A clinical close-up photograph of a skin lesion. A subject in their early 60s:
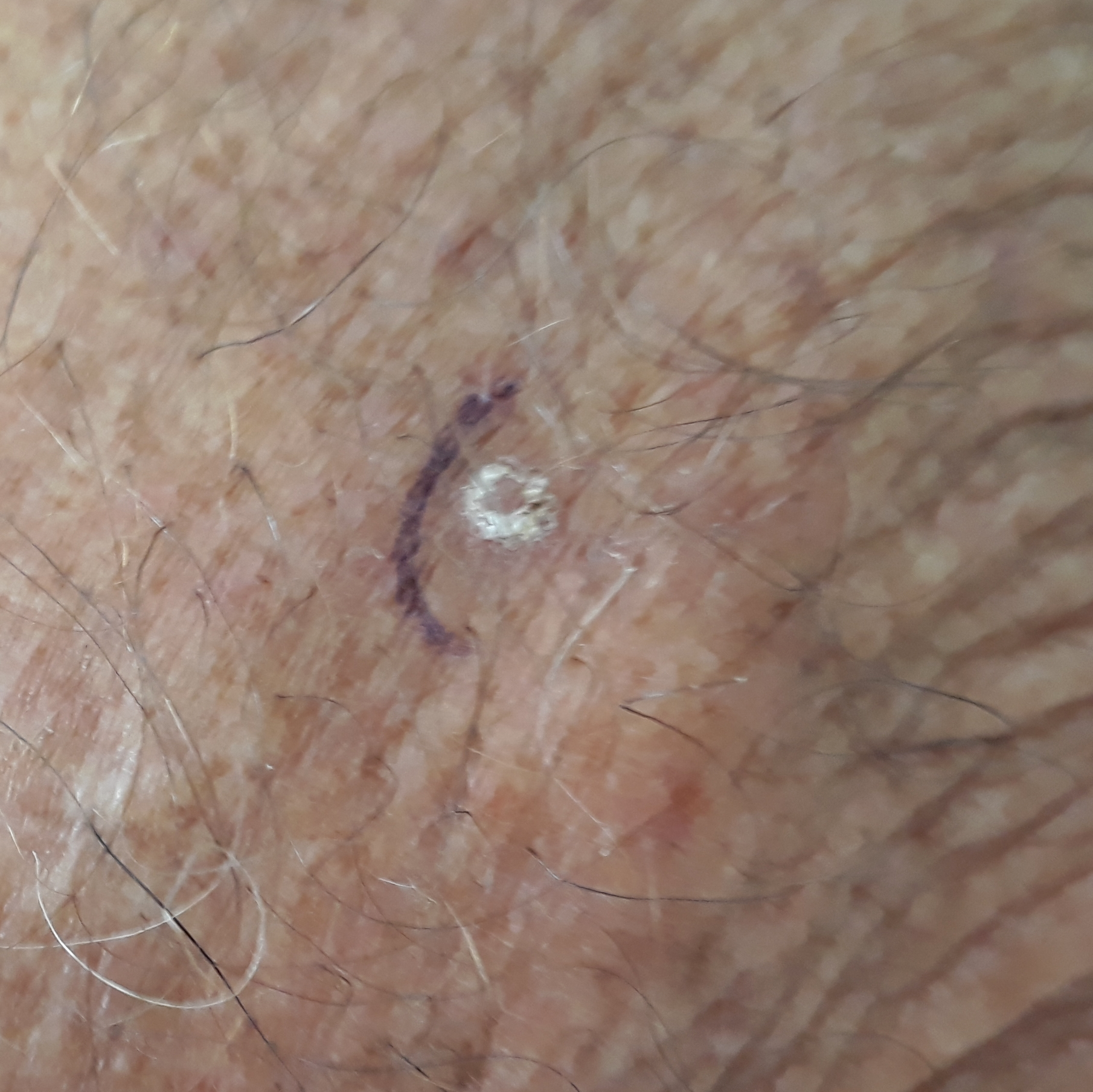site: a forearm
symptoms: itching, elevation / no growth, no pain
impression: actinic keratosis (clinical consensus)